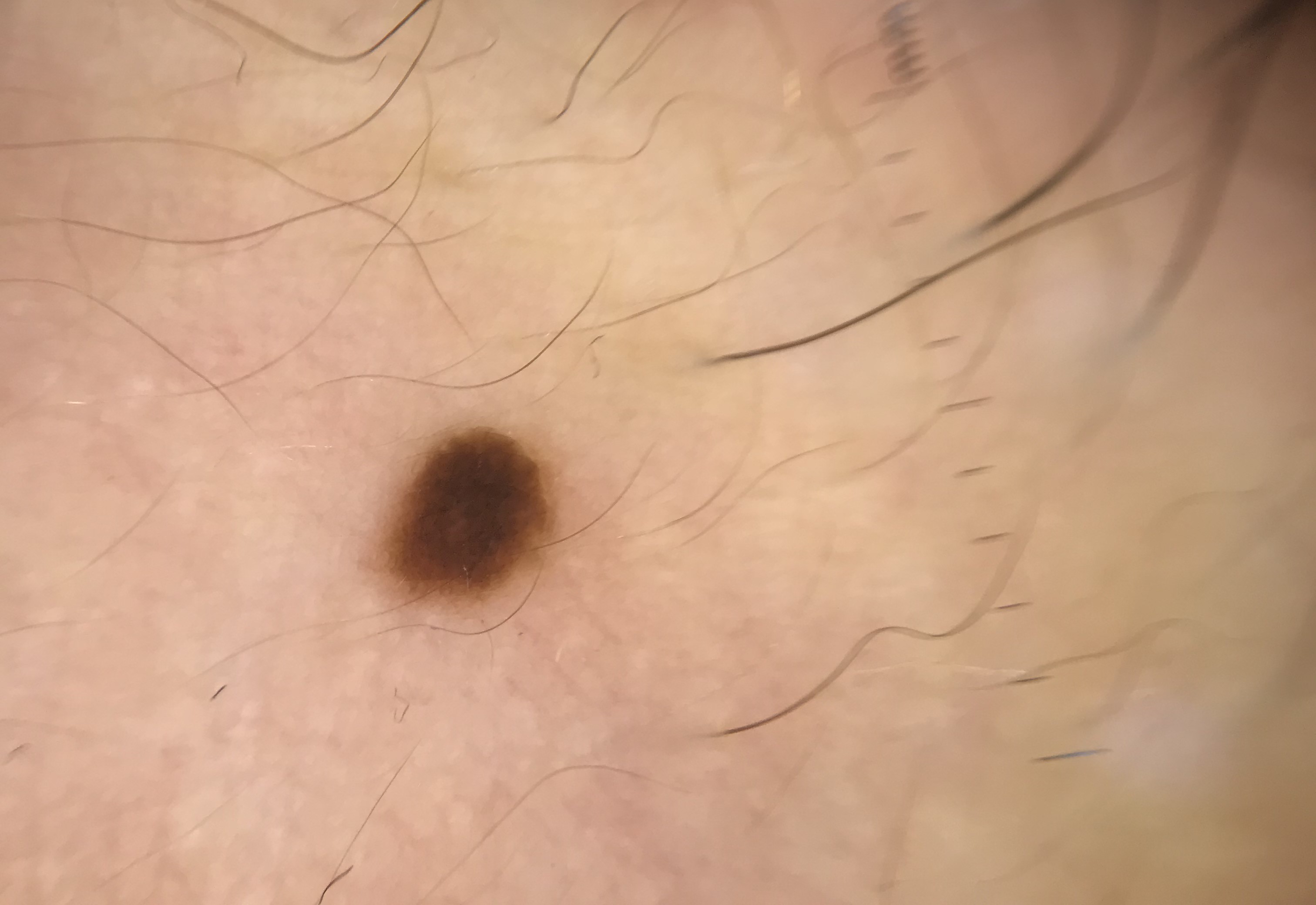image type = dermatoscopy | assessment = junctional nevus (expert consensus).